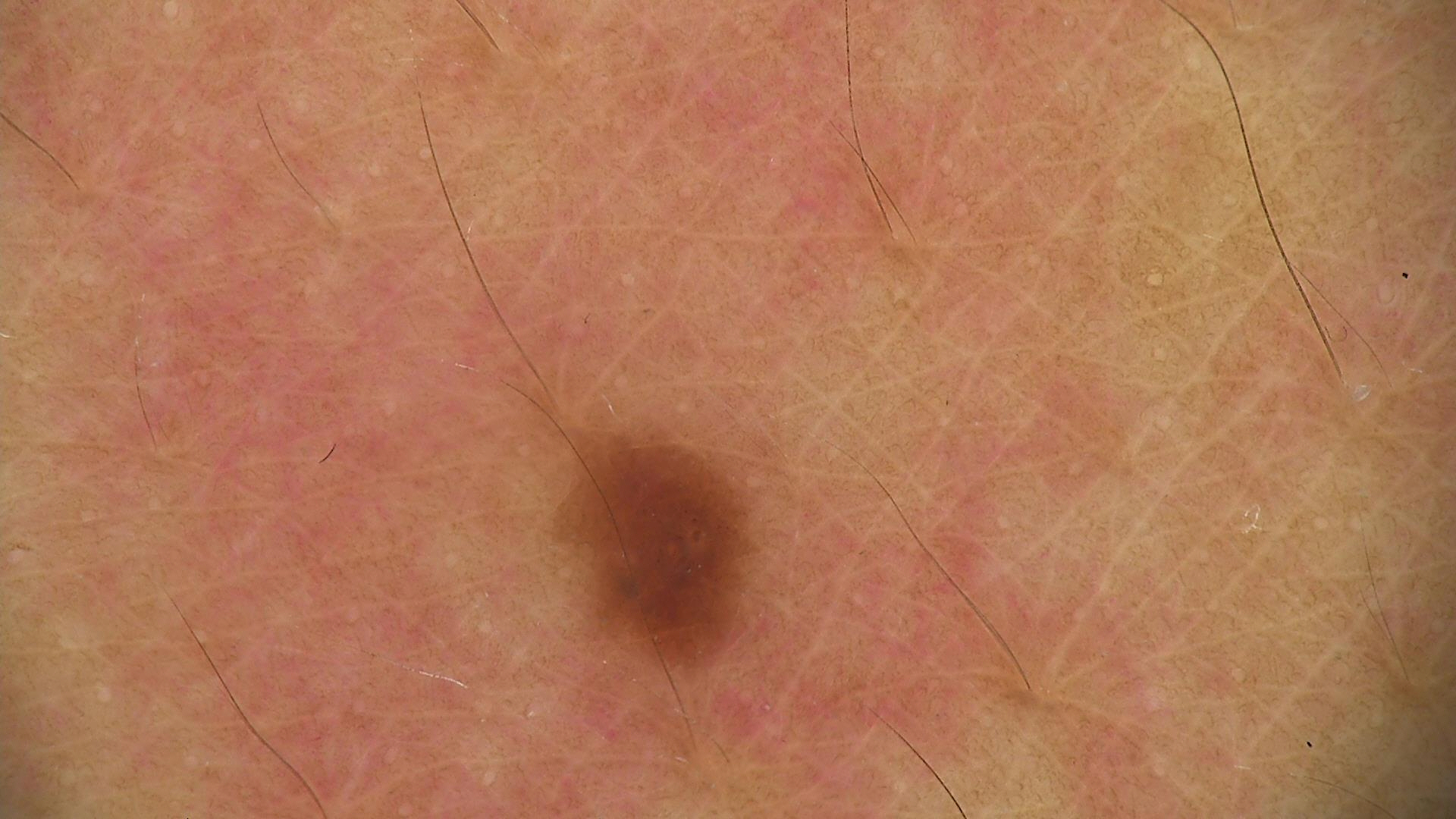label = junctional nevus (expert consensus).